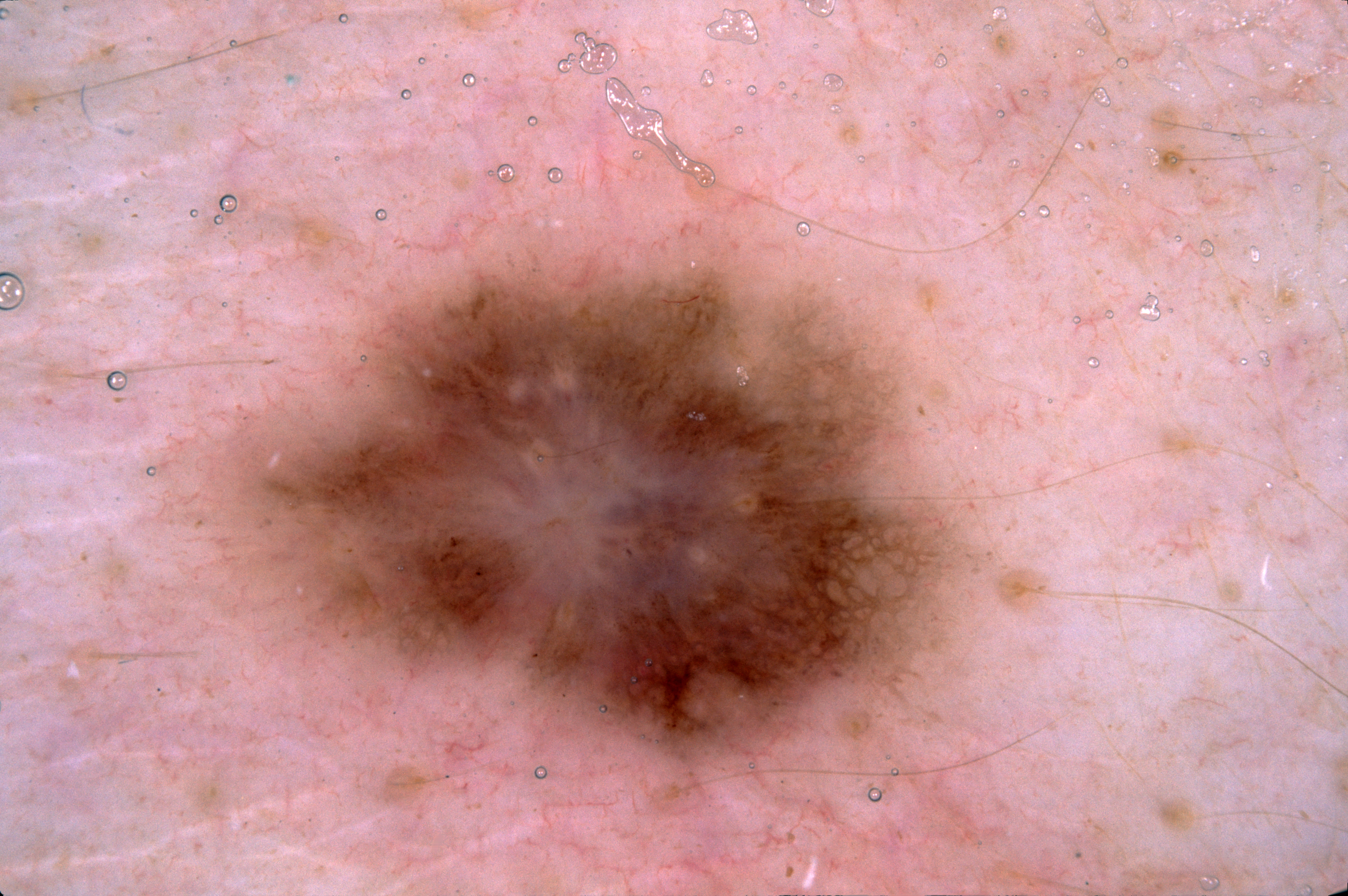  patient:
    sex: female
    age_approx: 30
  image:
    modality: dermoscopy
  lesion_location:
    bbox_xyxy:
      - 231
      - 248
      - 962
      - 814
  dermoscopic_features:
    present:
      - pigment network
    absent:
      - negative network
      - streaks
      - milia-like cysts
  diagnosis:
    name: melanocytic nevus
    malignancy: benign
    lineage: melanocytic
    provenance: clinical